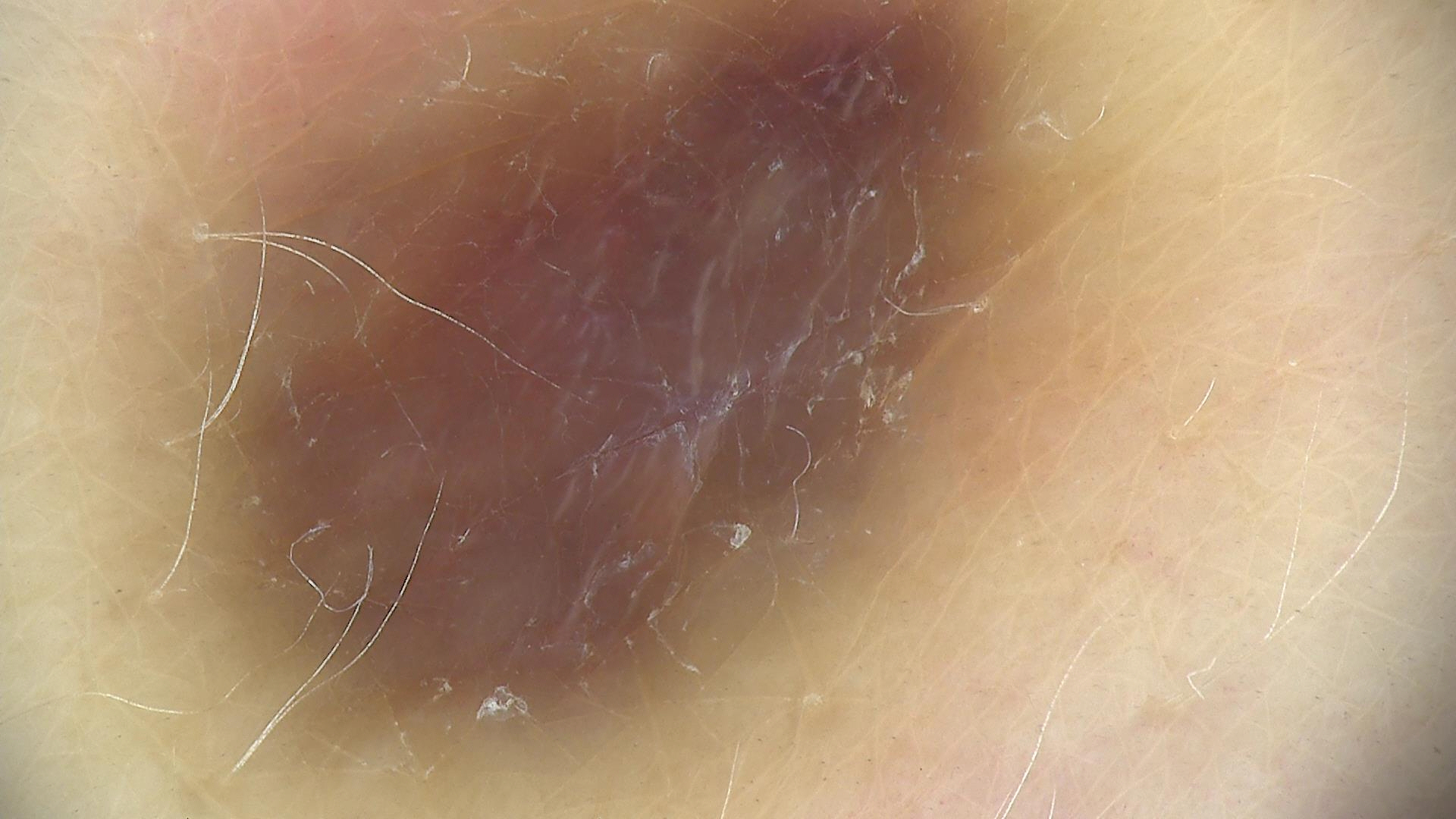imaging = dermoscopy; subtype = banal, dermal; diagnostic label = blue nevus (expert consensus).